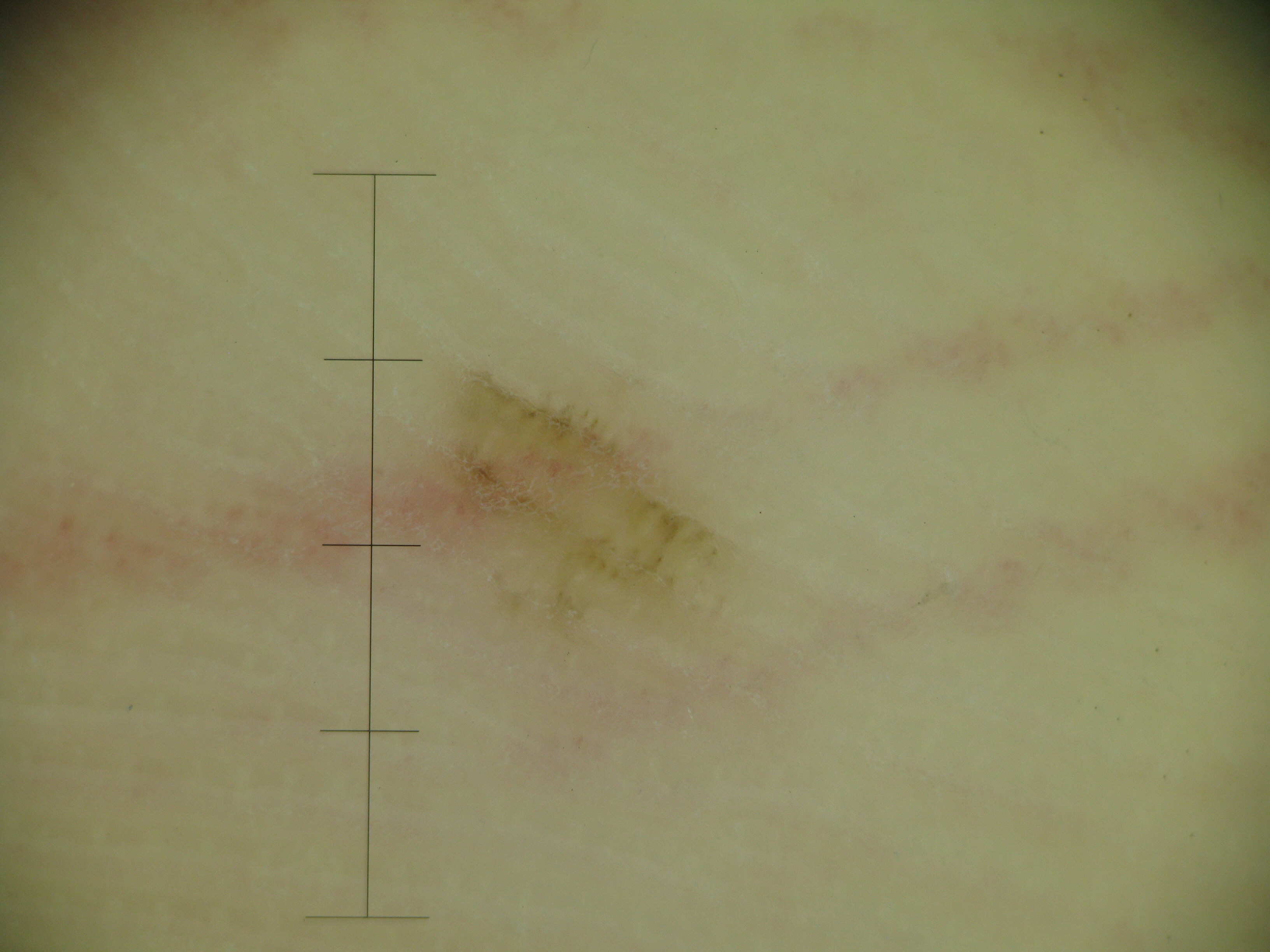image type: dermoscopy; diagnosis: acral junctional nevus (expert consensus).